A male patient aged 51 · the chart notes prior malignancy (patient or family), pesticide exposure, no prior skin cancer (patient or family), and no alcohol use · a clinical photograph of a skin lesion:
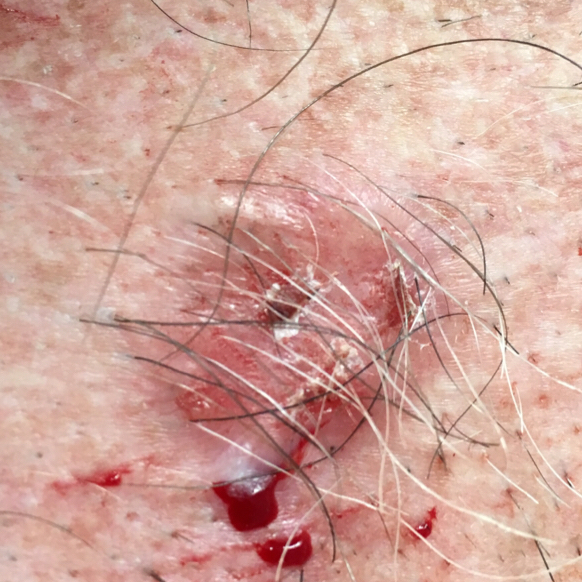The lesion involves the chest.
The lesion measures 15 × 15 mm.
The patient describes that the lesion has changed, has grown, and has bled.
Biopsy-confirmed as a basal cell carcinoma.